The lesion involves the arm and leg; this image was taken at an angle: 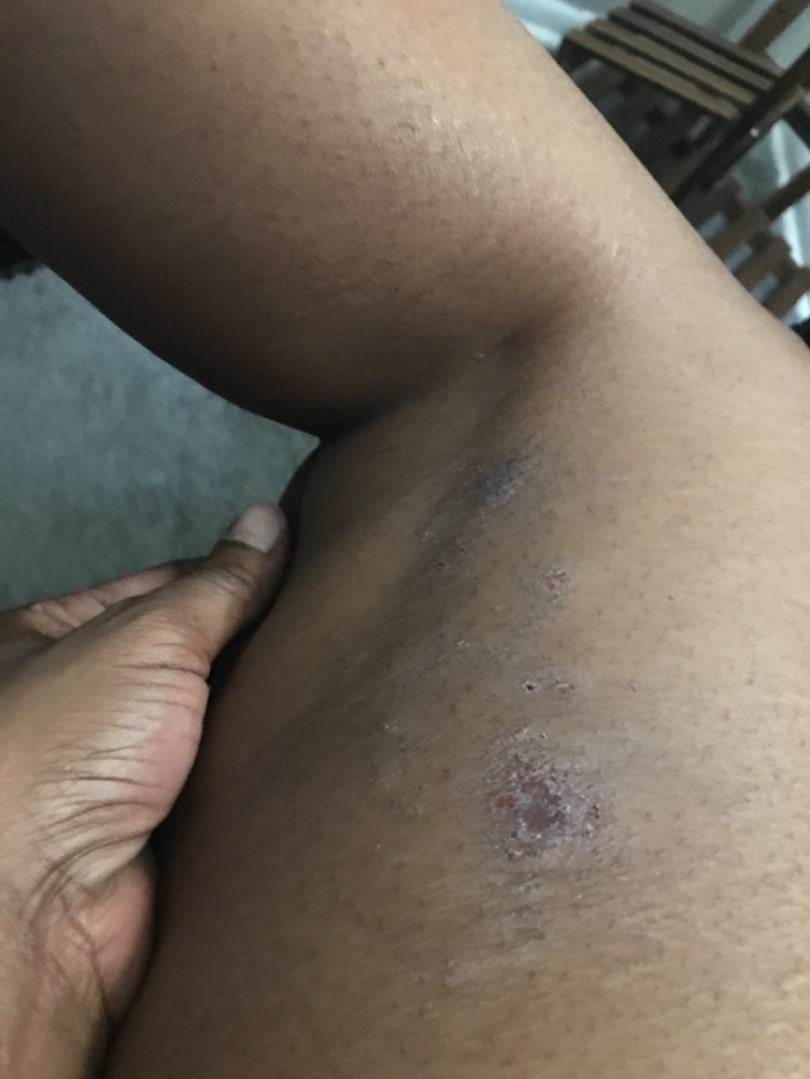  differential:
    leading:
      - Eczema